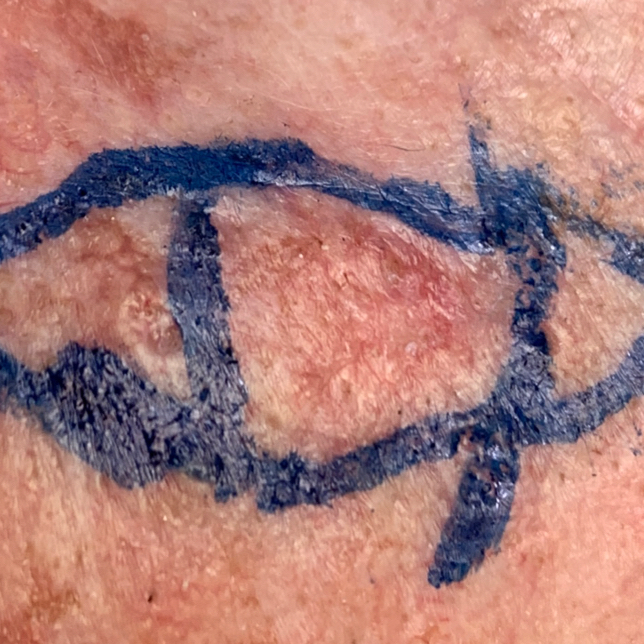Q: Who is the patient?
A: male, in their early 70s
Q: What is the anatomic site?
A: the face
Q: What did the workup show?
A: squamous cell carcinoma (biopsy-proven)